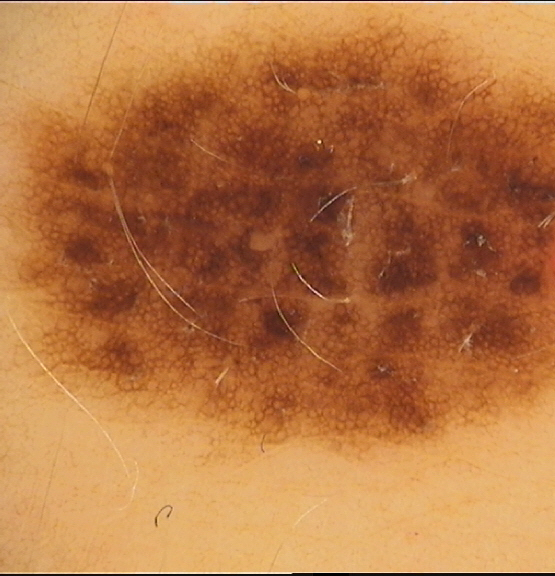Labeled as a dysplastic junctional nevus.